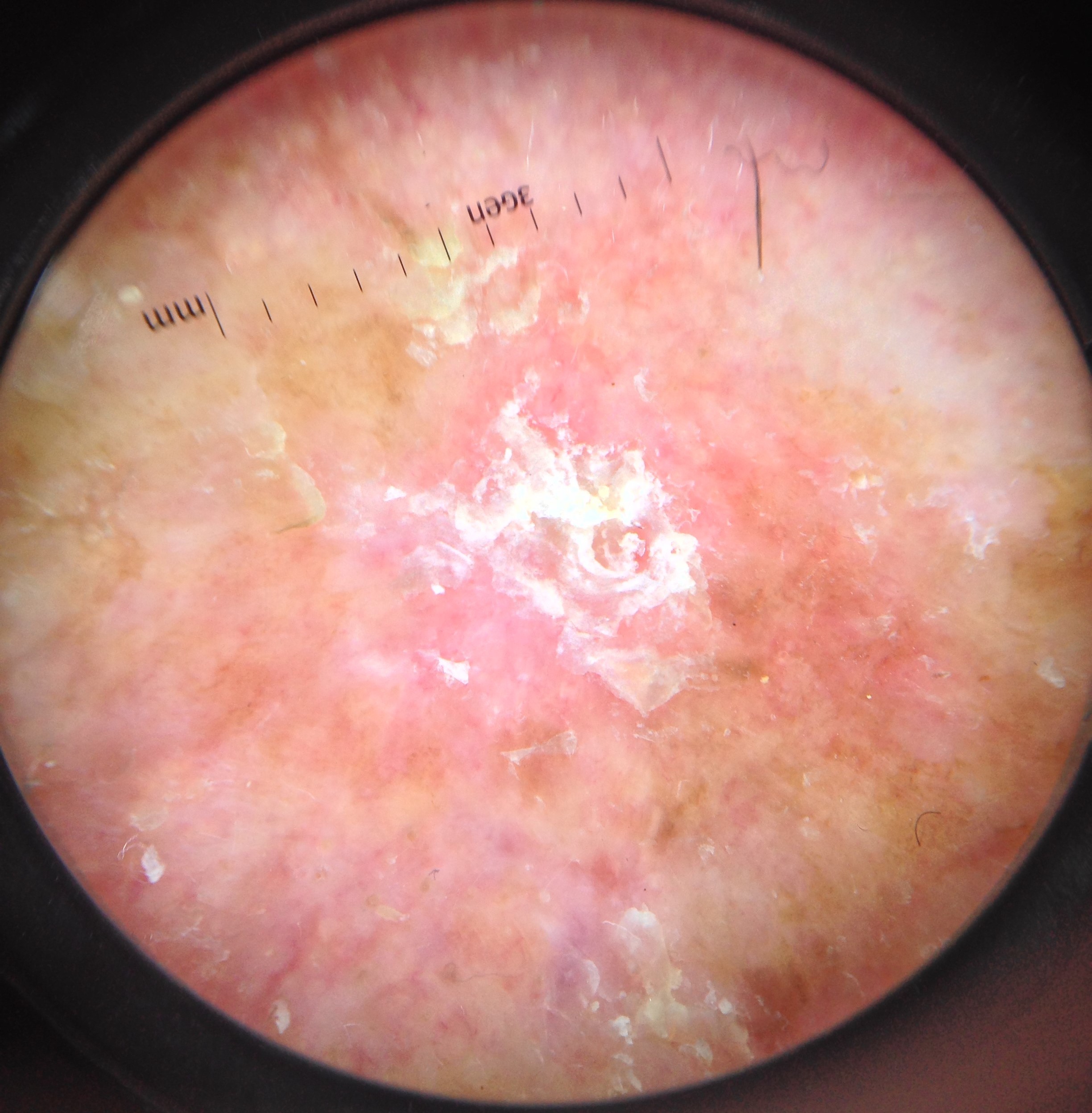Q: What kind of lesion is this?
A: keratinocytic
Q: What did the workup show?
A: squamous cell carcinoma (biopsy-proven)